A female subject 48 years old. Recorded as Fitzpatrick III. A smartphone photograph of a skin lesion. The chart notes prior skin cancer (patient or family):
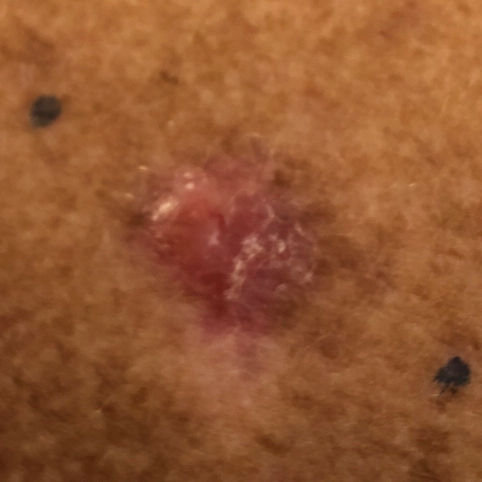lesion size: 12 × 8 mm; symptoms: itching, elevation; diagnosis: basal cell carcinoma (biopsy-proven).